The patient reported no systemic symptoms; the condition has been present for less than one week; the patient considered this a rash; located on the arm; Fitzpatrick II; female contributor, age 30–39; symptoms reported: bleeding and itching; the lesion is described as raised or bumpy; this image was taken at a distance: 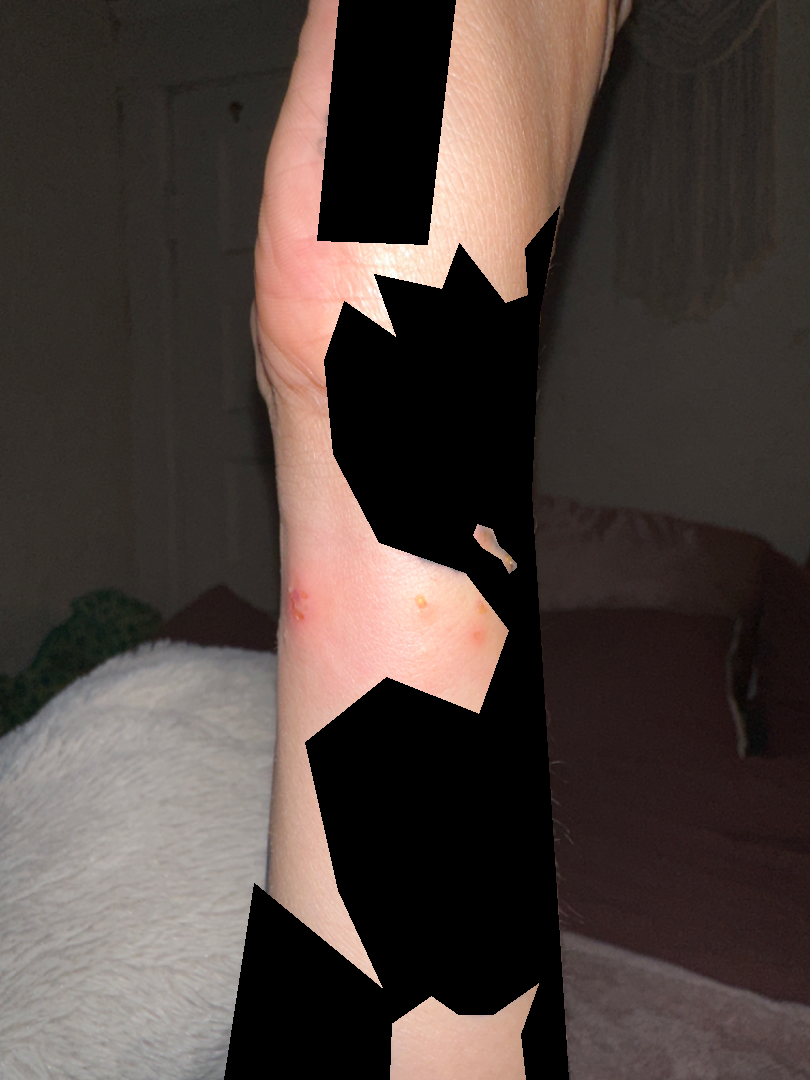The reviewing panel's impression was: Insect Bite and Impetigo were considered with similar weight; less probable is Contact dermatitis; a remote consideration is Herpes Simplex; lower on the differential is Acute dermatitis, NOS; less likely is Allergic Contact Dermatitis.